Close-up view · the lesion is described as rough or flaky · the condition has been present for one to three months · self-categorized by the patient as a rash · the lesion involves the back of the hand.
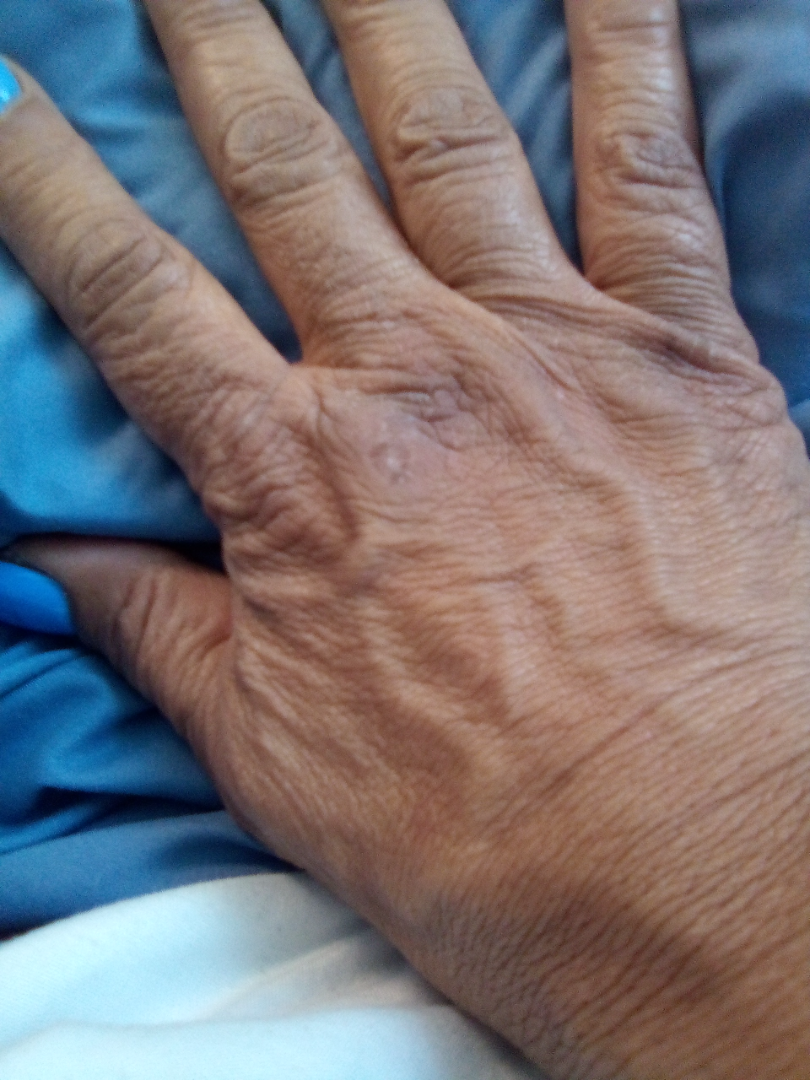Case summary:
- differential: favoring Verruca vulgaris; also raised was Lichen Simplex Chronicus